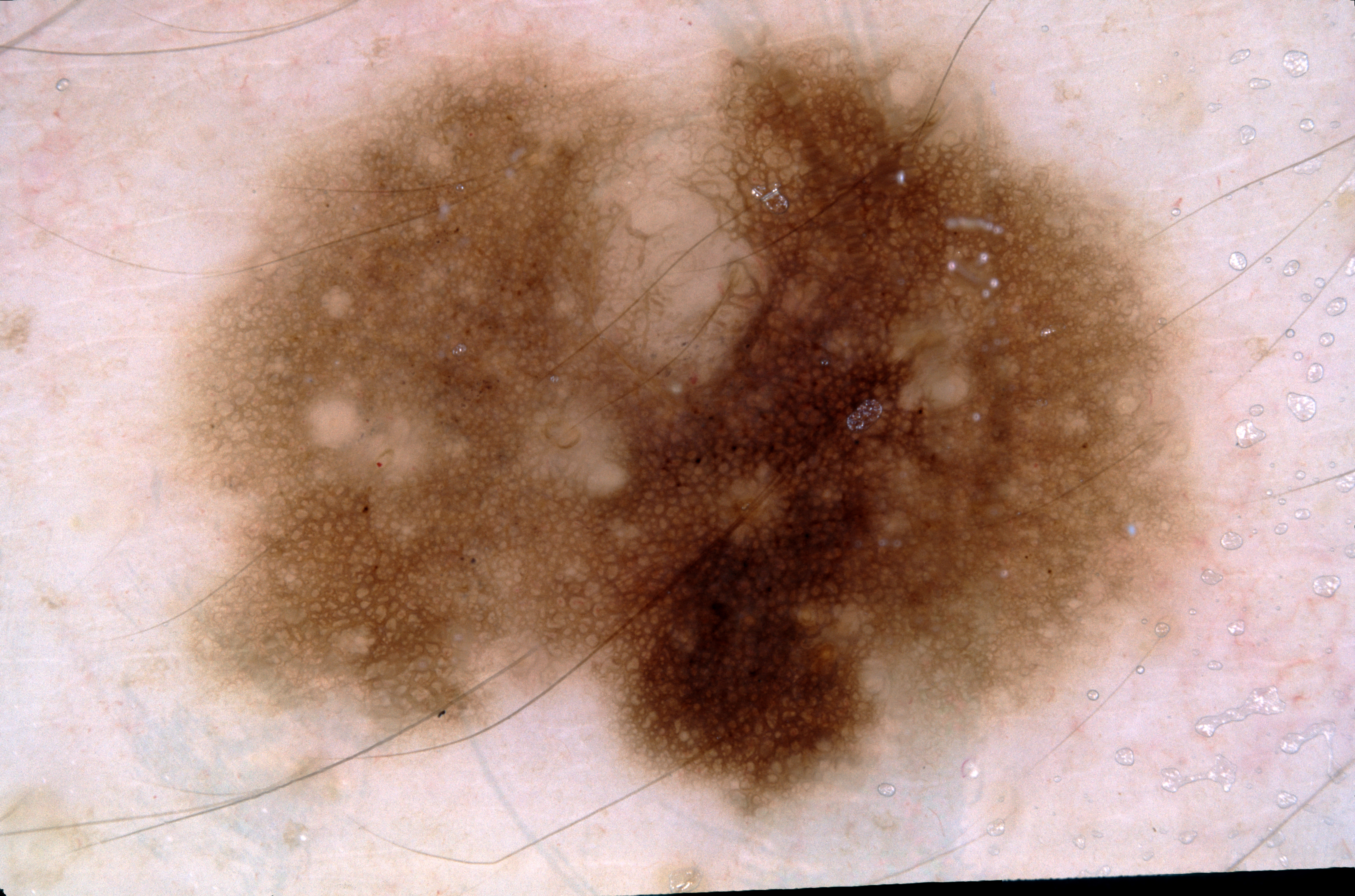A female patient approximately 35 years of age.
A dermoscopic image of a skin lesion.
Dermoscopy demonstrates milia-like cysts and pigment network.
The lesion occupies the region box(191, 31, 1190, 818).
The clinical diagnosis was a melanocytic nevus, a benign lesion.